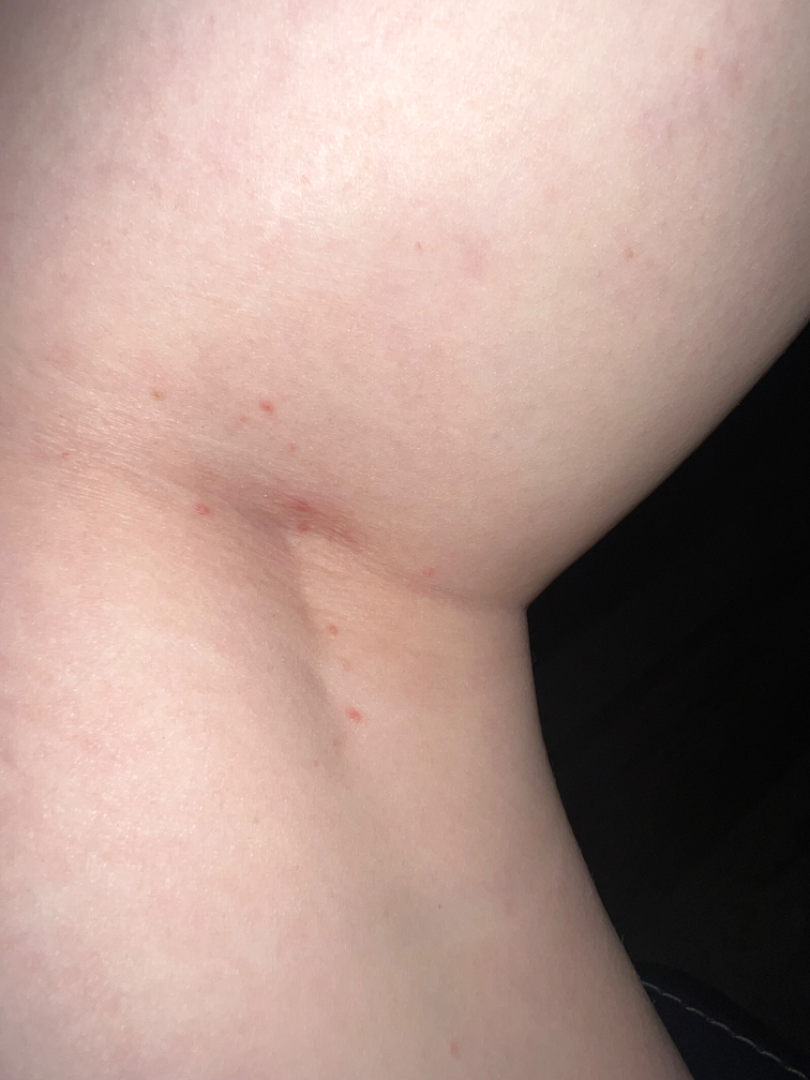Findings:
* patient's own categorization — a rash
* patient-reported symptoms — itching
* site — leg
* history — one to four weeks
* contributor — female, age 18–29
* view — close-up
* assessment — the leading consideration is Miliaria